A dermatoscopic image of a skin lesion: 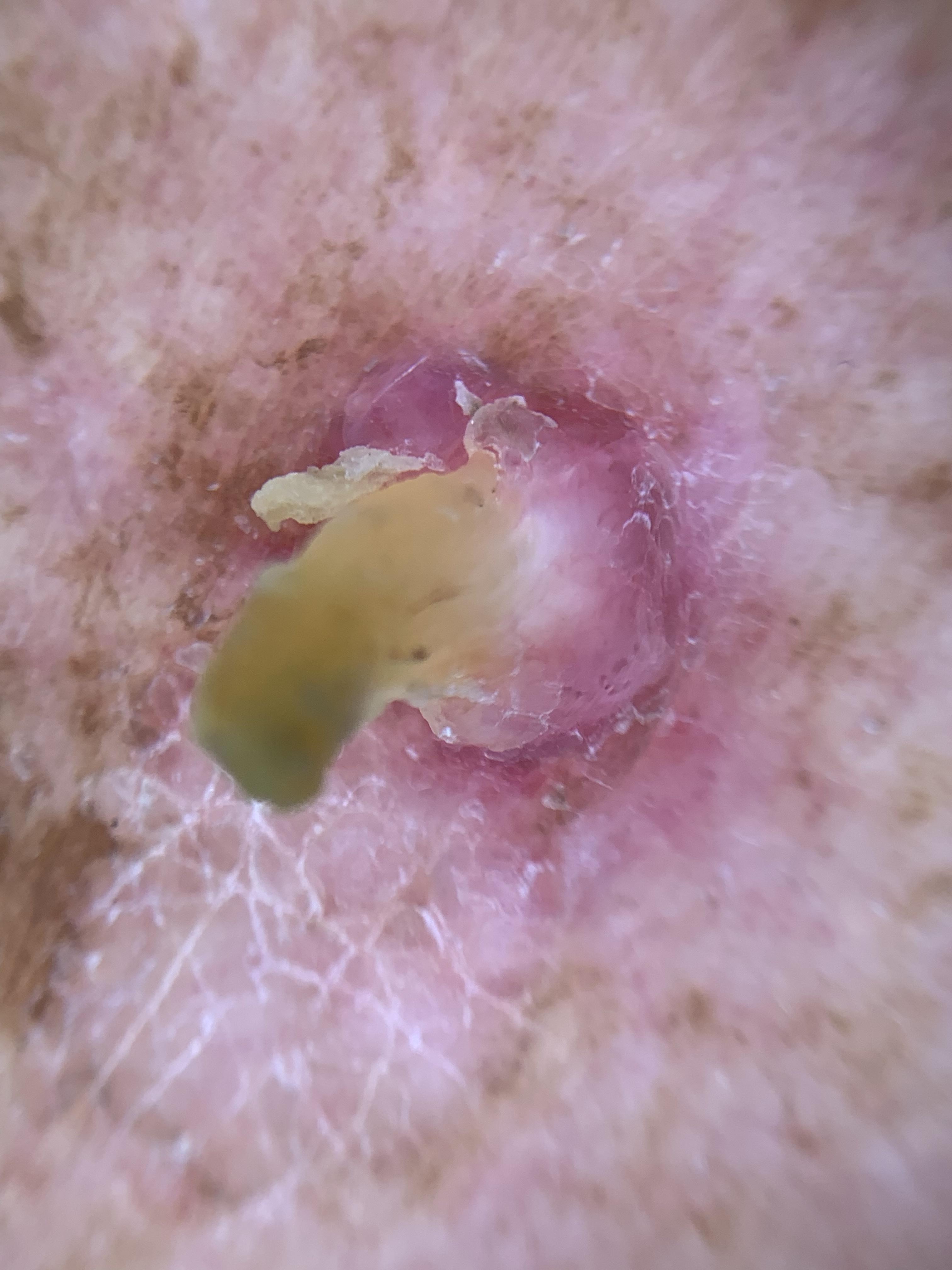<skin_lesion>
  <lesion_location>
    <region>the trunk</region>
    <detail>the anterior trunk</detail>
  </lesion_location>
  <diagnosis>
    <name>Squamous cell carcinoma</name>
    <malignancy>malignant</malignancy>
    <confirmation>histopathology</confirmation>
    <lineage>epidermal</lineage>
  </diagnosis>
</skin_lesion>